A male subject about 70 years old; Fitzpatrick phototype II; a dermatoscopic image of a skin lesion.
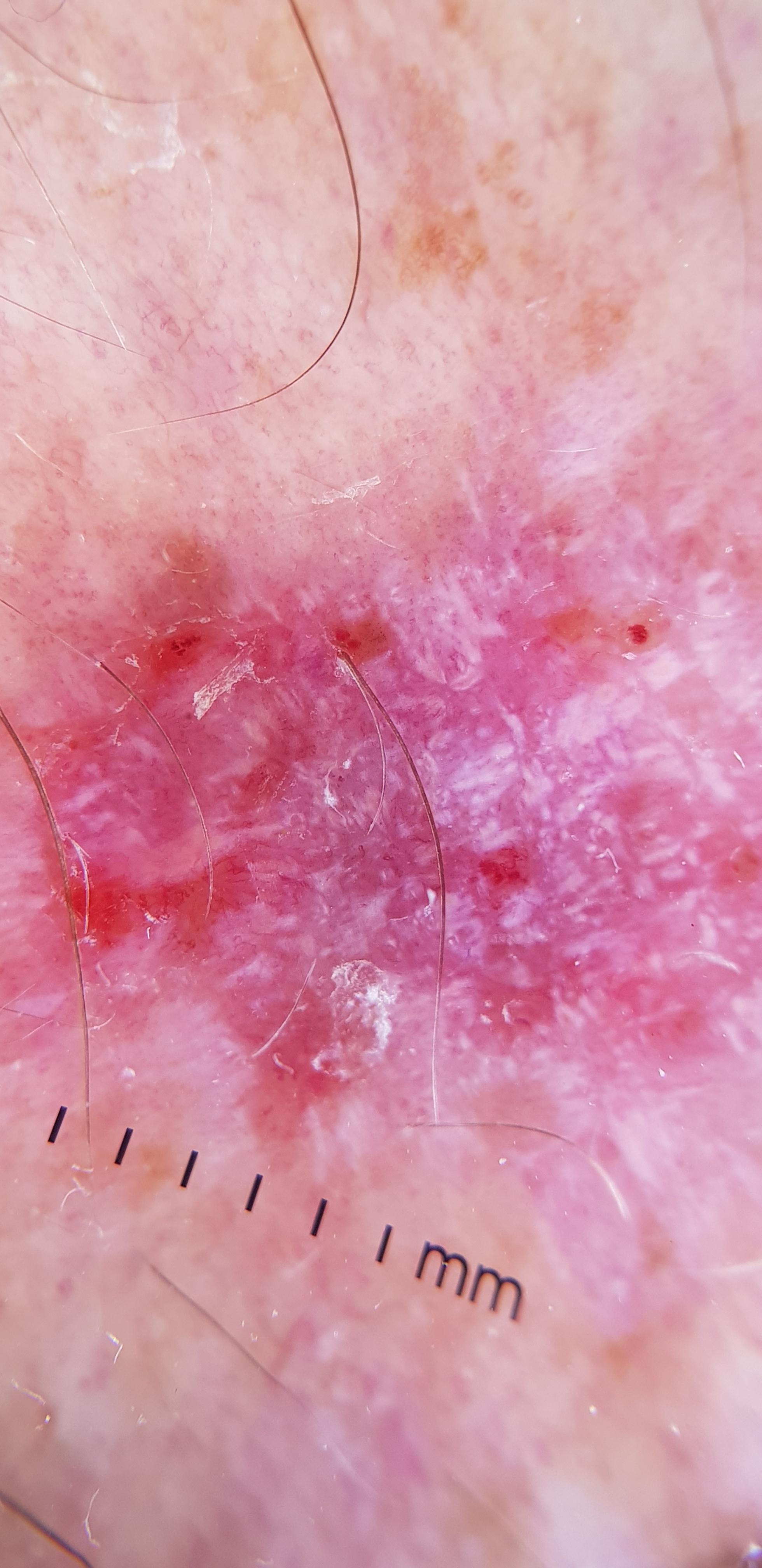anatomic site: a lower extremity
pathology: Squamous cell carcinoma (biopsy-proven)